Imaged for a research study, with no referral diagnosis recorded; the patient reports a prior organ transplant and immunosuppression; a female subject age 55; dermoscopy of a skin lesion; the patient describes having a moderate number of moles: 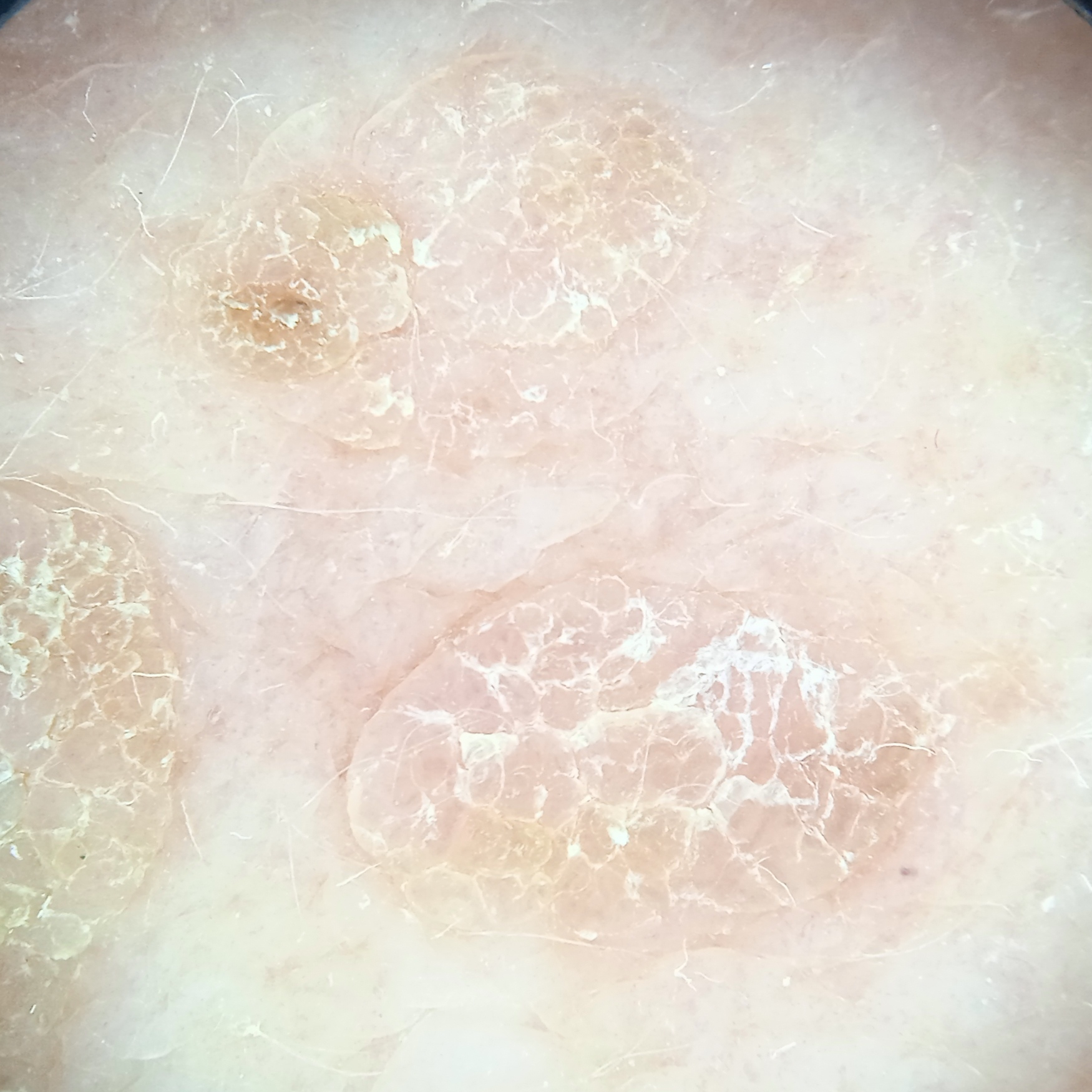Located on the back.
The lesion measures approximately 10.6 mm.
The dermatologists' assessment was a seborrheic keratosis.